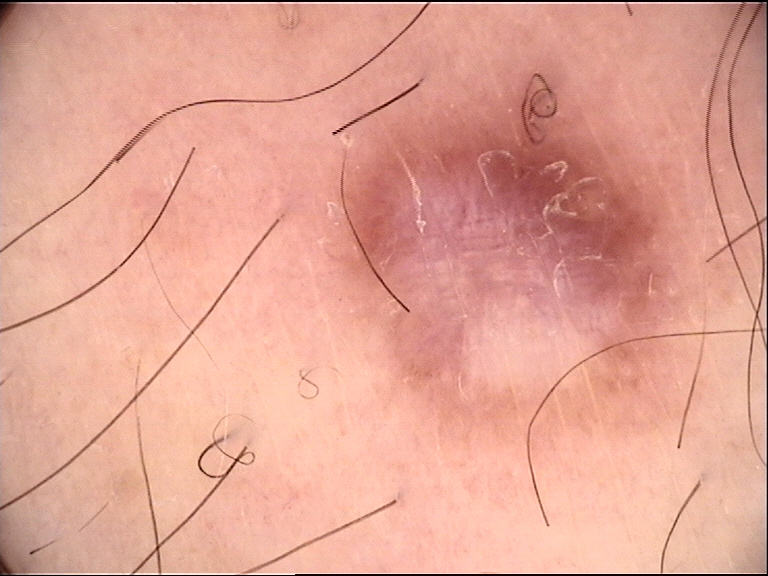{"image": "dermatoscopy", "lesion_type": {"main_class": "fibro-histiocytic"}, "diagnosis": {"name": "dermatofibroma", "code": "df", "malignancy": "benign", "super_class": "non-melanocytic", "confirmation": "expert consensus"}}